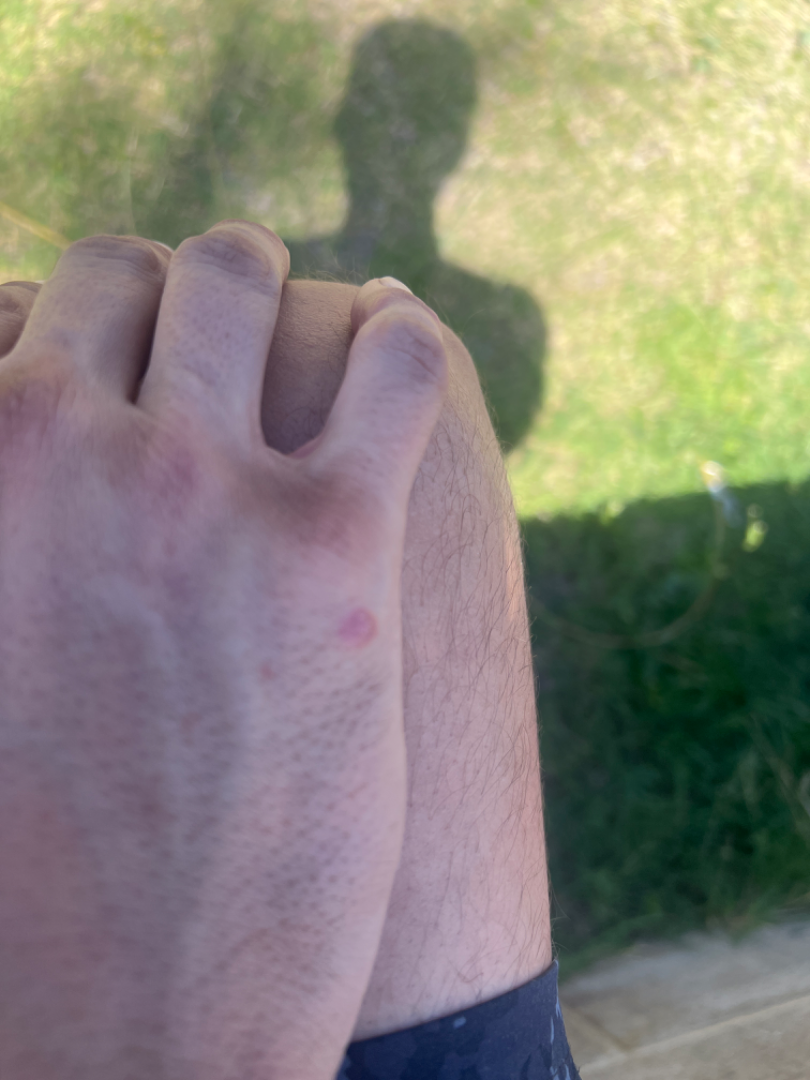Impression: On remote dermatologist review, most consistent with Actinic Keratosis; also raised was Prurigo nodularis.